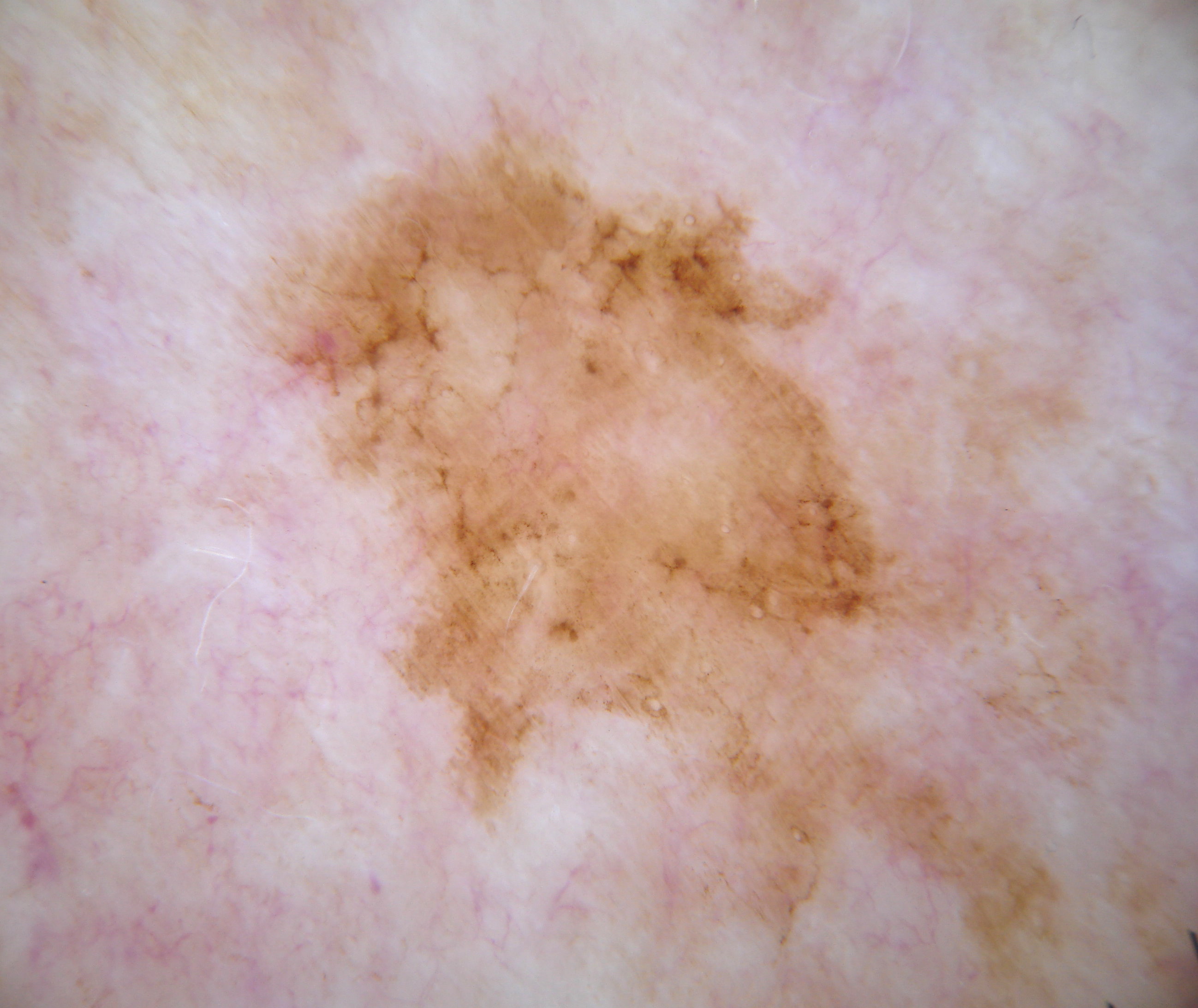A dermoscopic image of a skin lesion. Dermoscopy demonstrates no pigment network, negative network, milia-like cysts, globules, or streaks. The lesion's extent is [224,97,1123,1001]. A prominent lesion filling much of the field. Histopathological examination showed a melanoma, a skin cancer.